A male subject, aged approximately 60. A dermoscopy image of a single skin lesion: 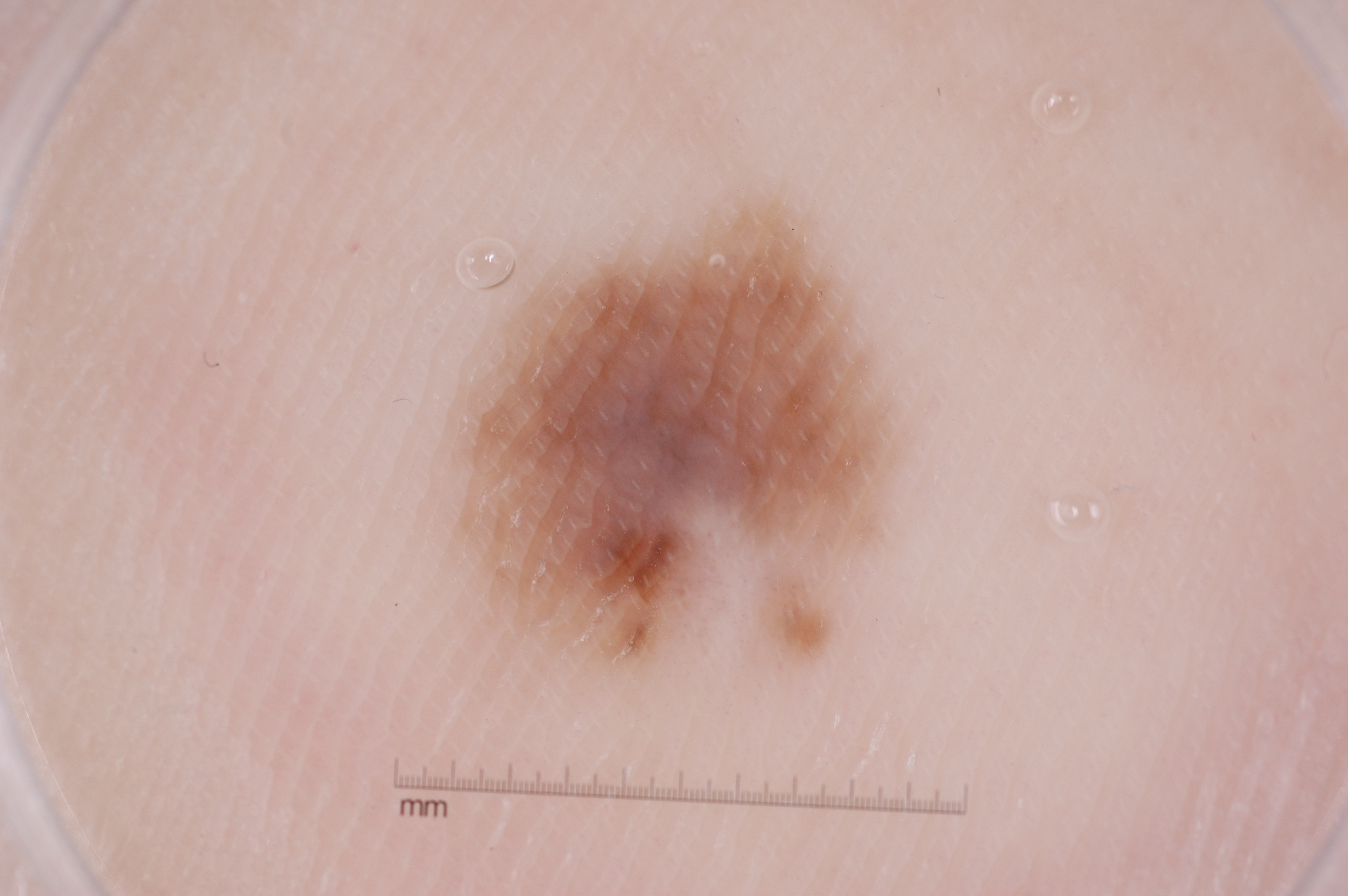Dermoscopy demonstrates no negative network, pigment network, streaks, or milia-like cysts. With coordinates (x1, y1, x2, y2), the lesion is bounded by [445, 194, 901, 682]. The clinical diagnosis was a melanocytic nevus, a benign skin lesion.